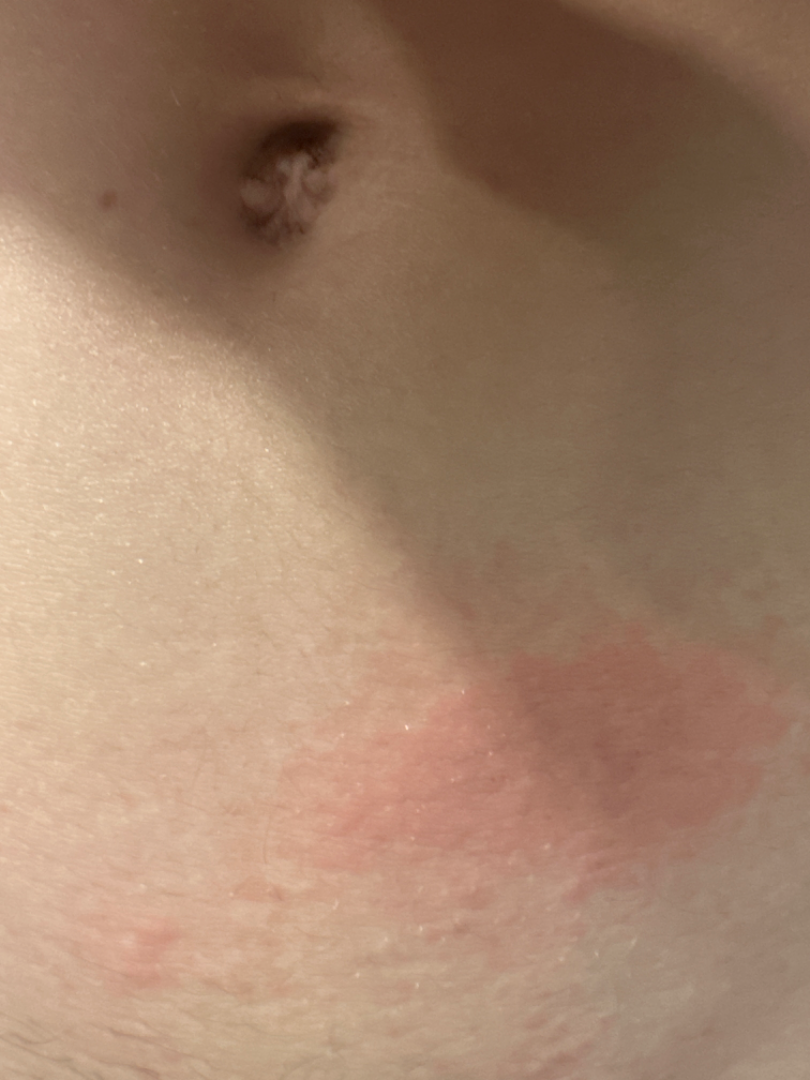{
  "differential": {
    "leading": [
      "Urticaria"
    ],
    "considered": [
      "Acute dermatitis, NOS"
    ],
    "unlikely": [
      "Allergic Contact Dermatitis",
      "Eczema"
    ]
  }
}